Dermoscopy of a skin lesion.
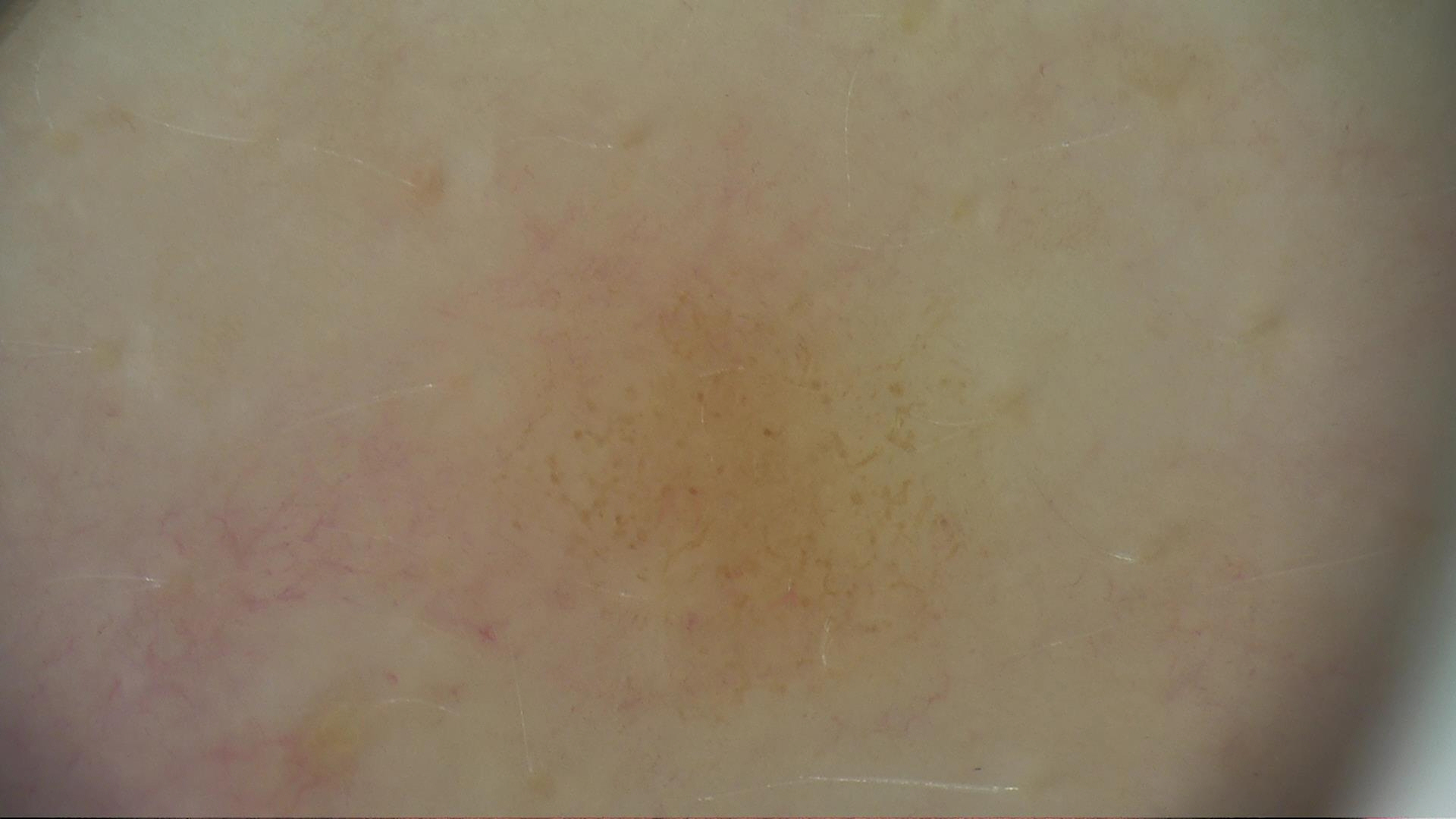Case:
* class · dysplastic junctional nevus (expert consensus)